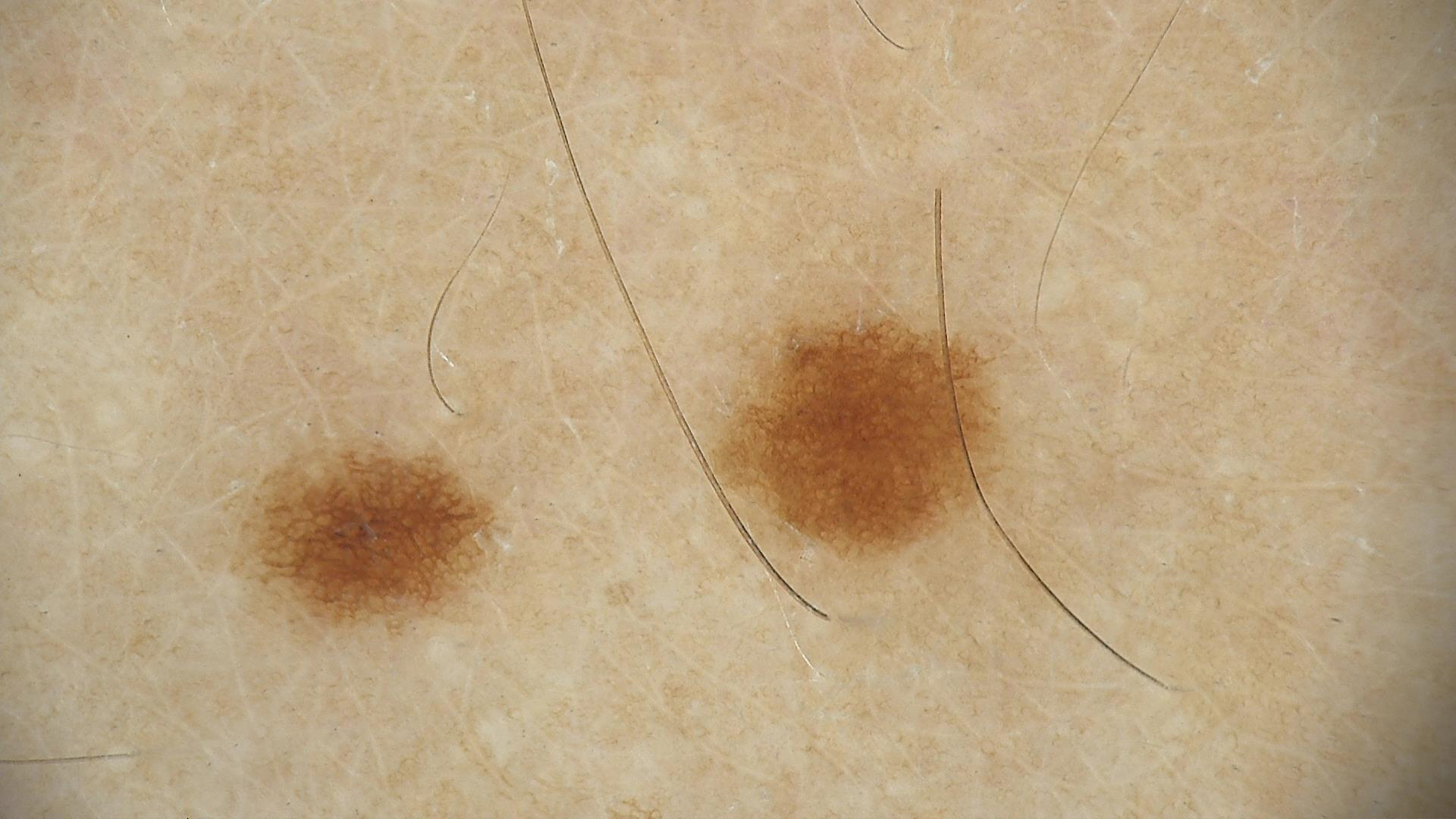Impression: Consistent with a dysplastic junctional nevus.